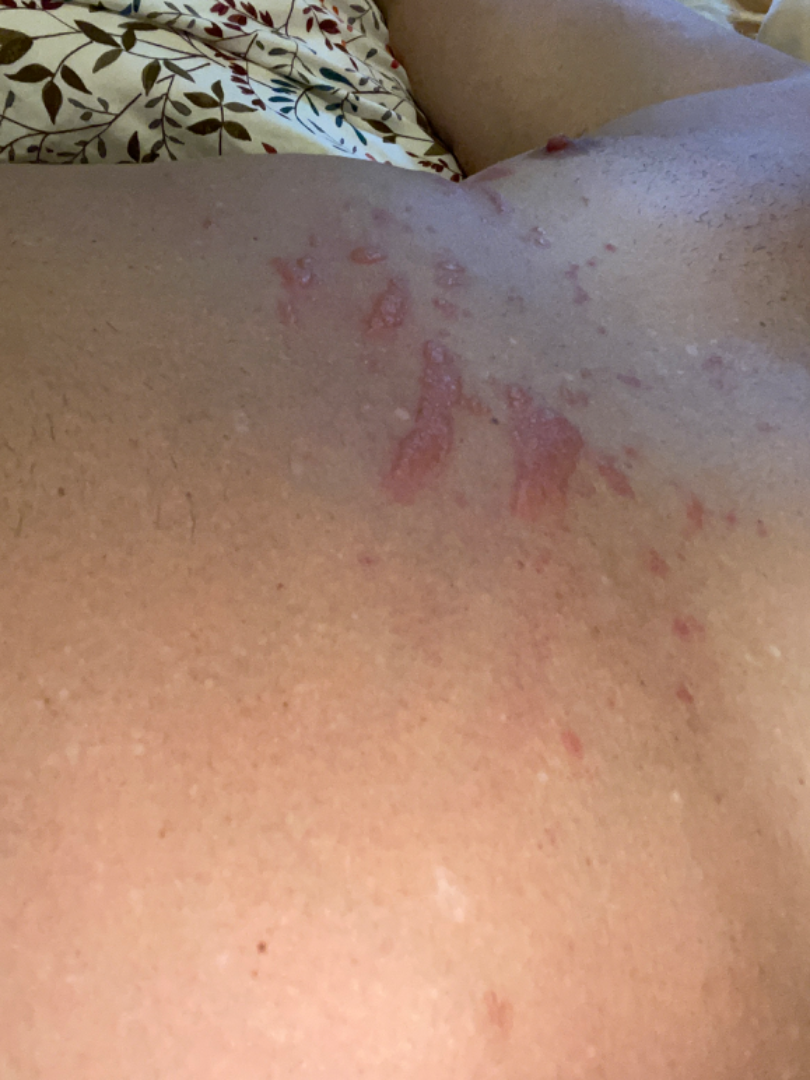differential:
  leading:
    - Allergic Contact Dermatitis
  considered:
    - Herpes Zoster